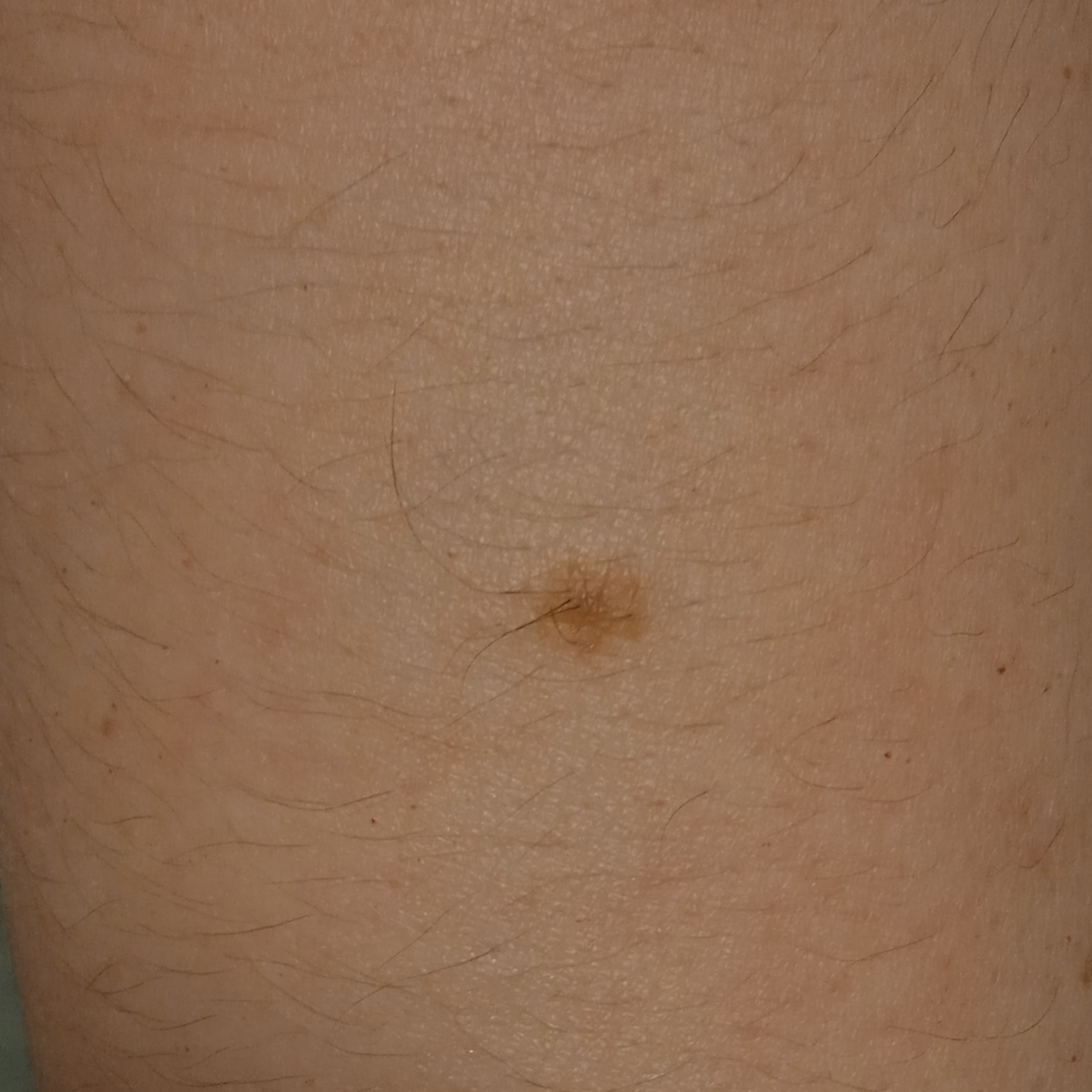patient: female, 35 years old; image: clinical photograph; risk factors: no personal history of skin cancer, no personal history of cancer; clinical context: research study (no referral diagnosis); nevus count: a moderate number of melanocytic nevi; location: an arm; assessment: melanocytic nevus (dermatologist consensus).